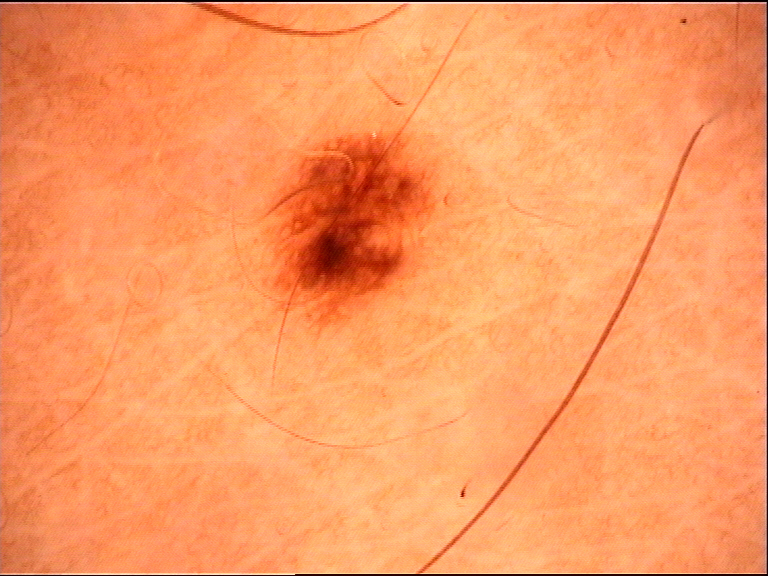– modality · dermoscopy
– diagnosis · dysplastic junctional nevus (expert consensus)